Contact-polarized dermoscopy of a skin lesion:
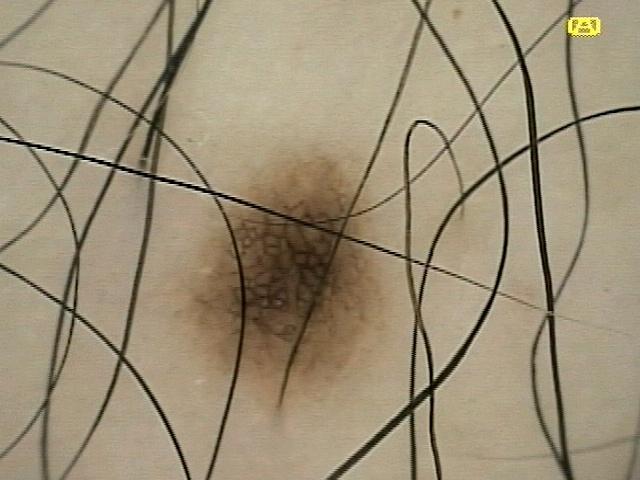– location: the trunk (the anterior trunk)
– impression: Nevus